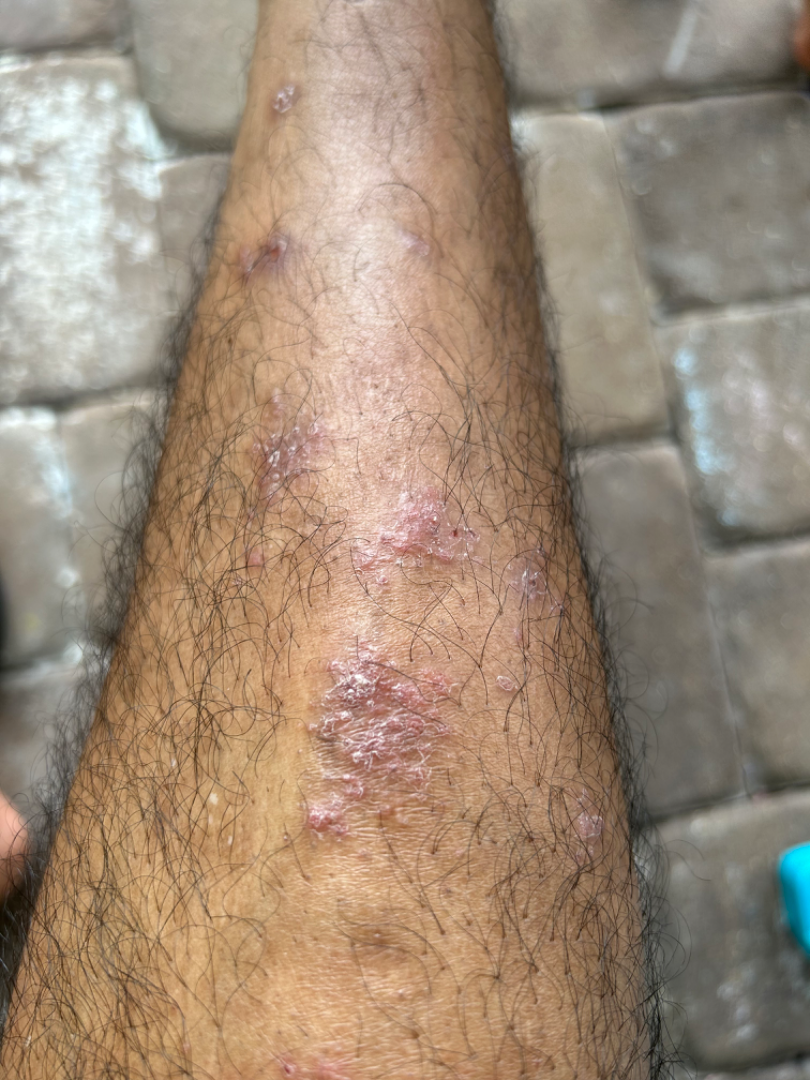This is a close-up image. The lesion involves the back of the torso and leg. Self-categorized by the patient as a rash. Human graders estimated Monk skin tone scale 5. The patient reports the condition has been present for more than one year. Texture is reported as flat and rough or flaky. The subject is male. The patient reports bothersome appearance, itching and enlargement. The patient also reports joint pain. On remote dermatologist review: Lichen planus/lichenoid eruption (0.55); Kaposi's sarcoma of skin (0.27); Psoriasis (0.18).